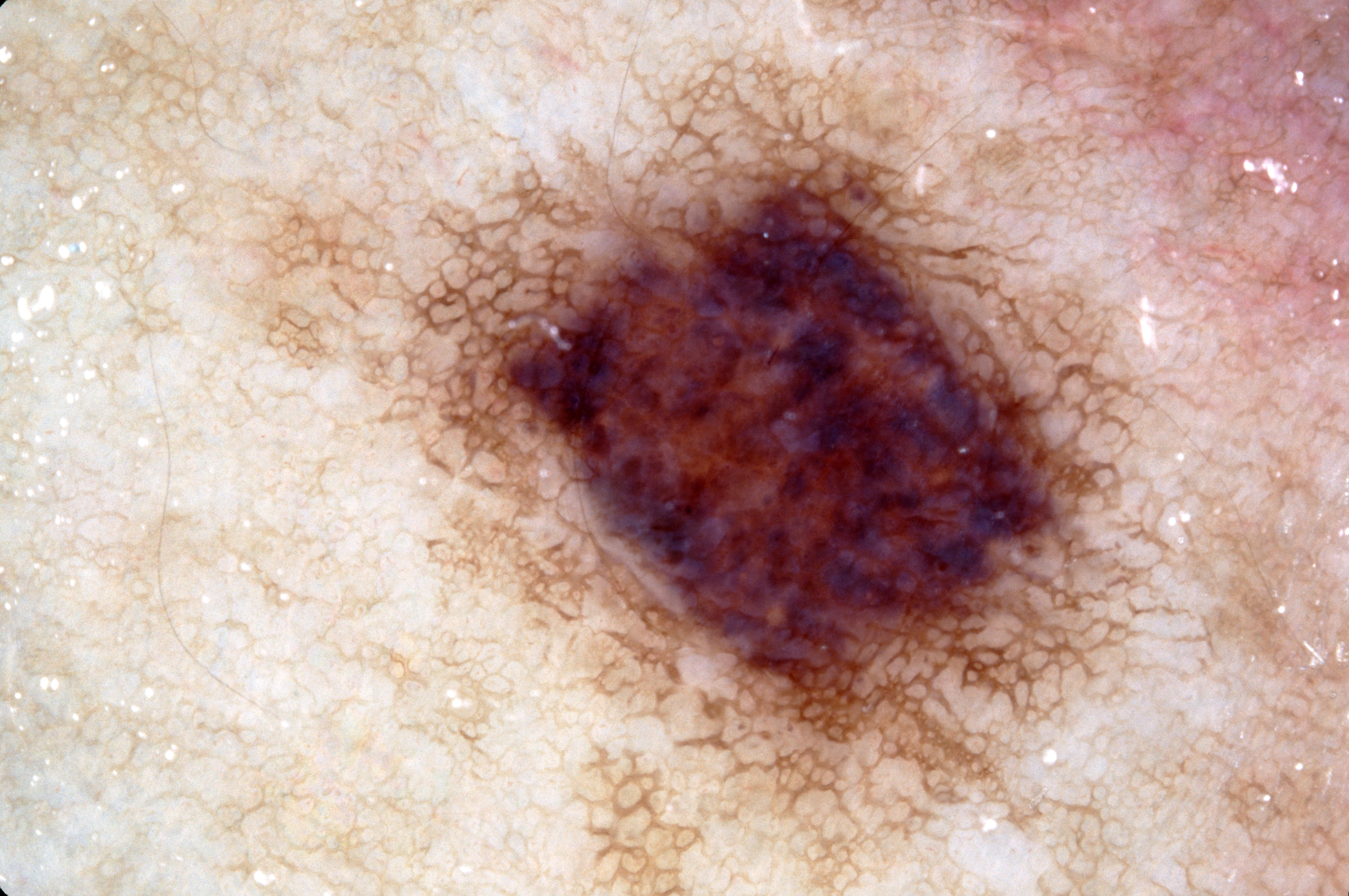modality = dermoscopy of a skin lesion
location = [226, 1, 1231, 894]
lesion extent = ~48% of the field
dermoscopic features = pigment network; absent: streaks, negative network, and milia-like cysts
diagnostic label = a melanocytic nevus